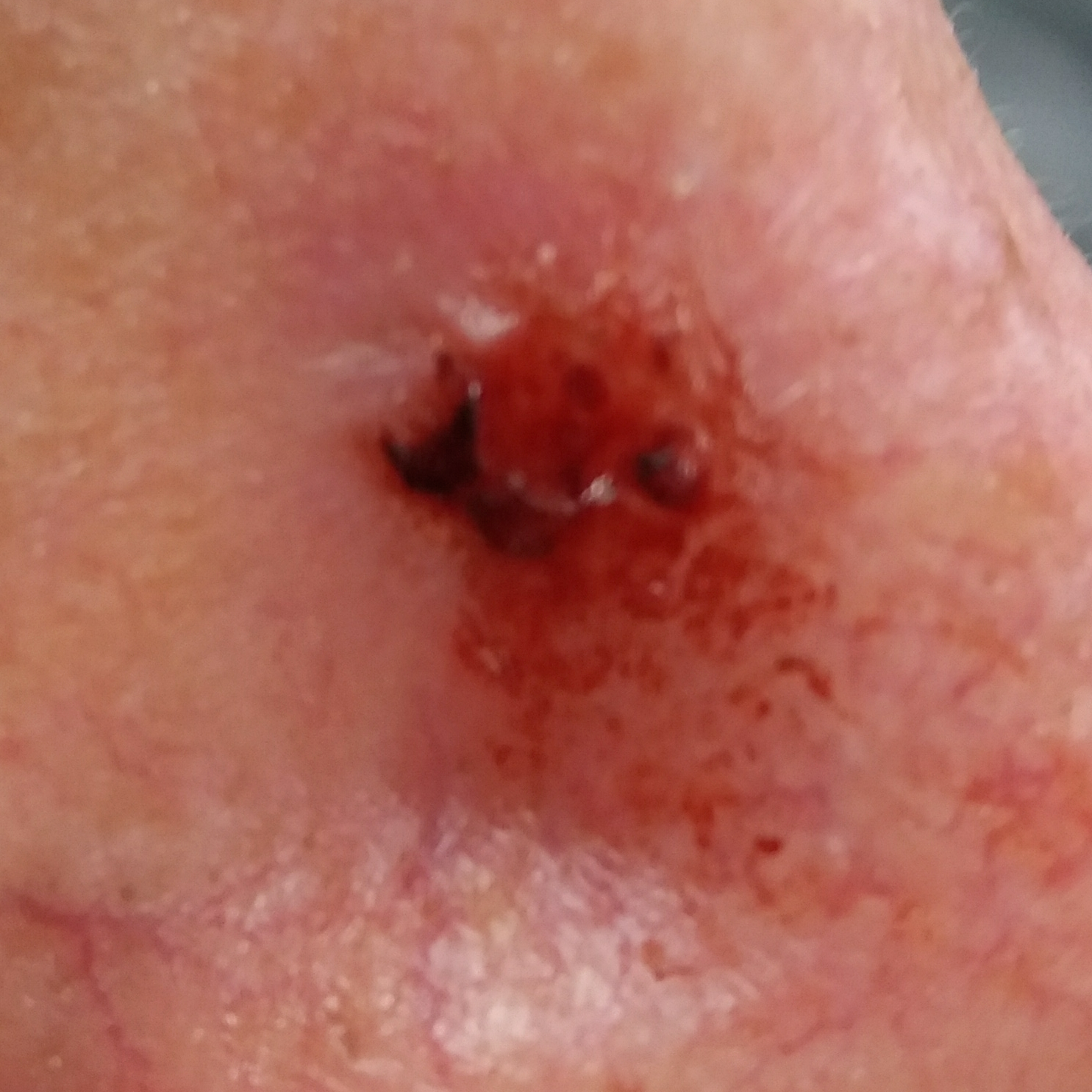Q: What is the imaging modality?
A: clinical photograph
Q: Tell me about the patient.
A: female, in their early 40s
Q: What does the exposure history note?
A: prior skin cancer (patient or family)
Q: Where on the body is the lesion?
A: the nose
Q: How large is the lesion?
A: 10 × 7 mm
Q: What does the patient describe?
A: bleeding, itching, growth / no pain, no elevation
Q: What is this lesion?
A: basal cell carcinoma (biopsy-proven)